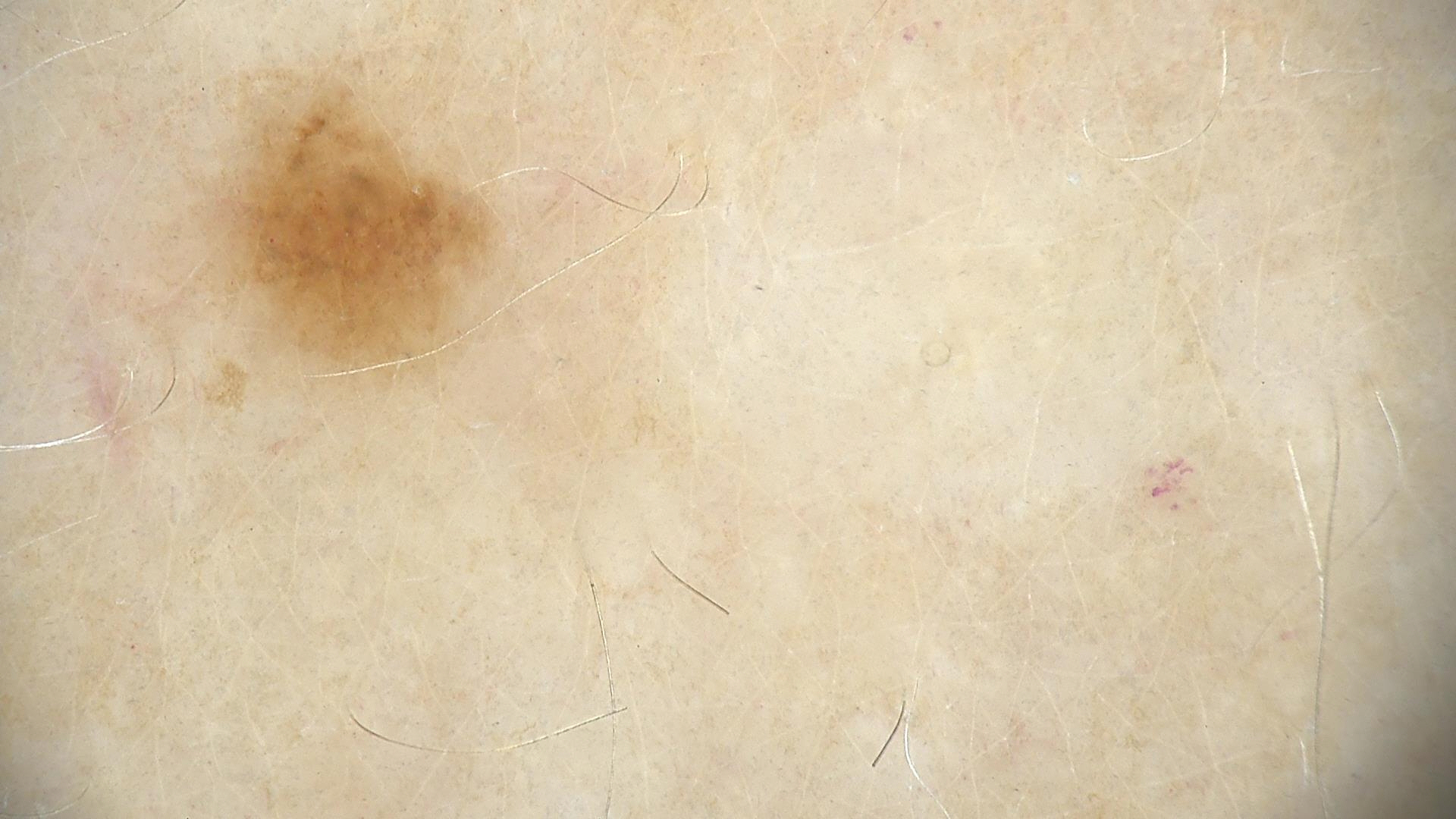* modality · dermatoscopy
* class · dysplastic junctional nevus (expert consensus)